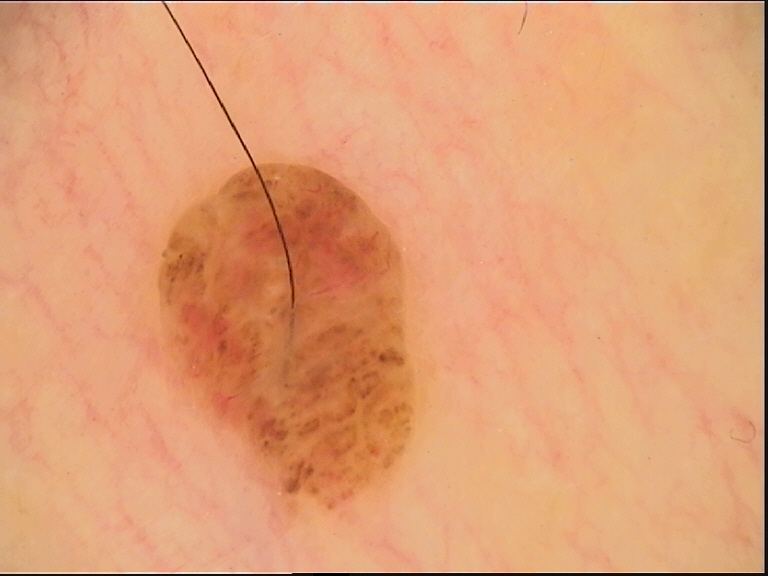This is a banal lesion.
Classified as a dermal nevus.